Skin tone: Fitzpatrick V, the photograph is a close-up of the affected area:
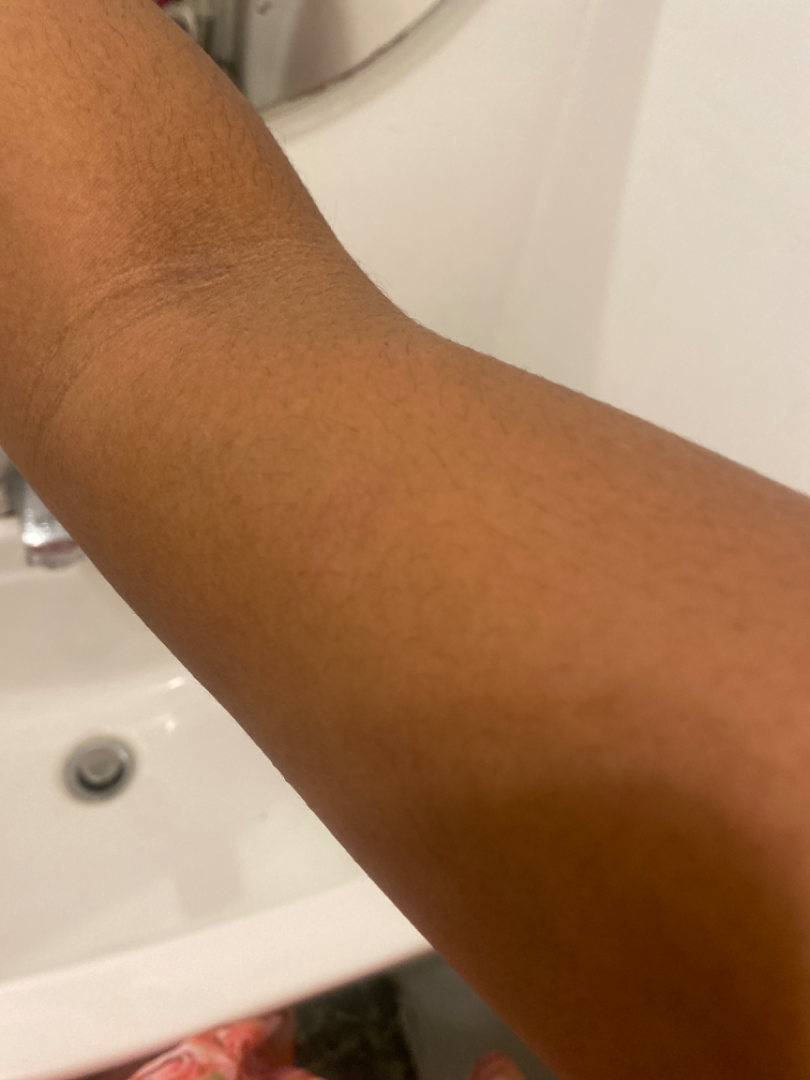Assessment: No skin condition was discernible on photographic review.